The affected area is the arm · this is a close-up image.
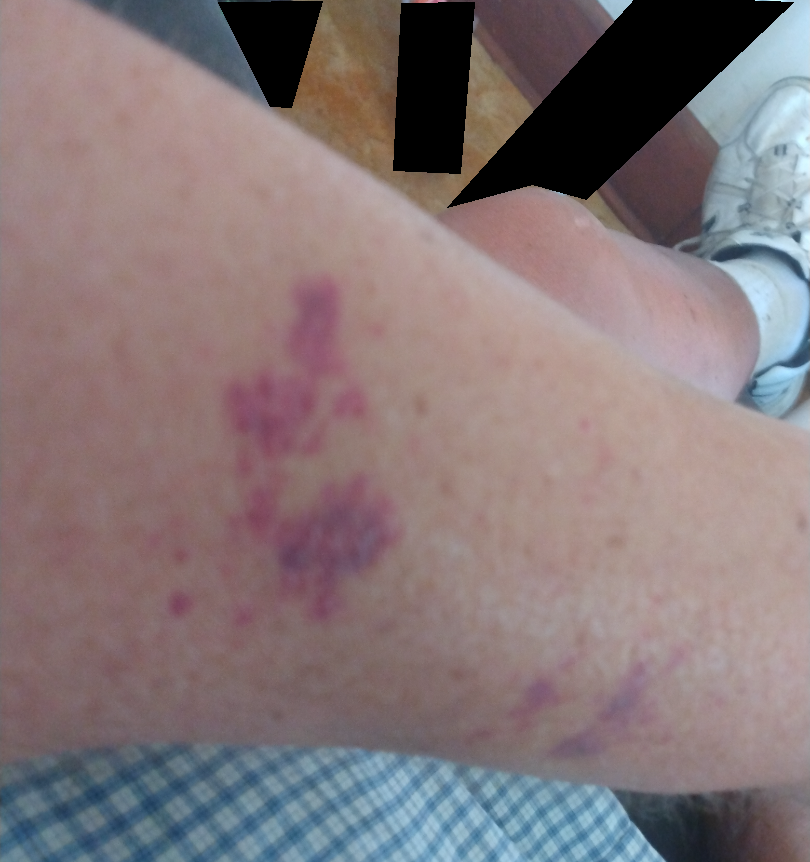Diagnostic features were not clearly distinguishable in this photograph. Present for one to four weeks. Texture is reported as flat.